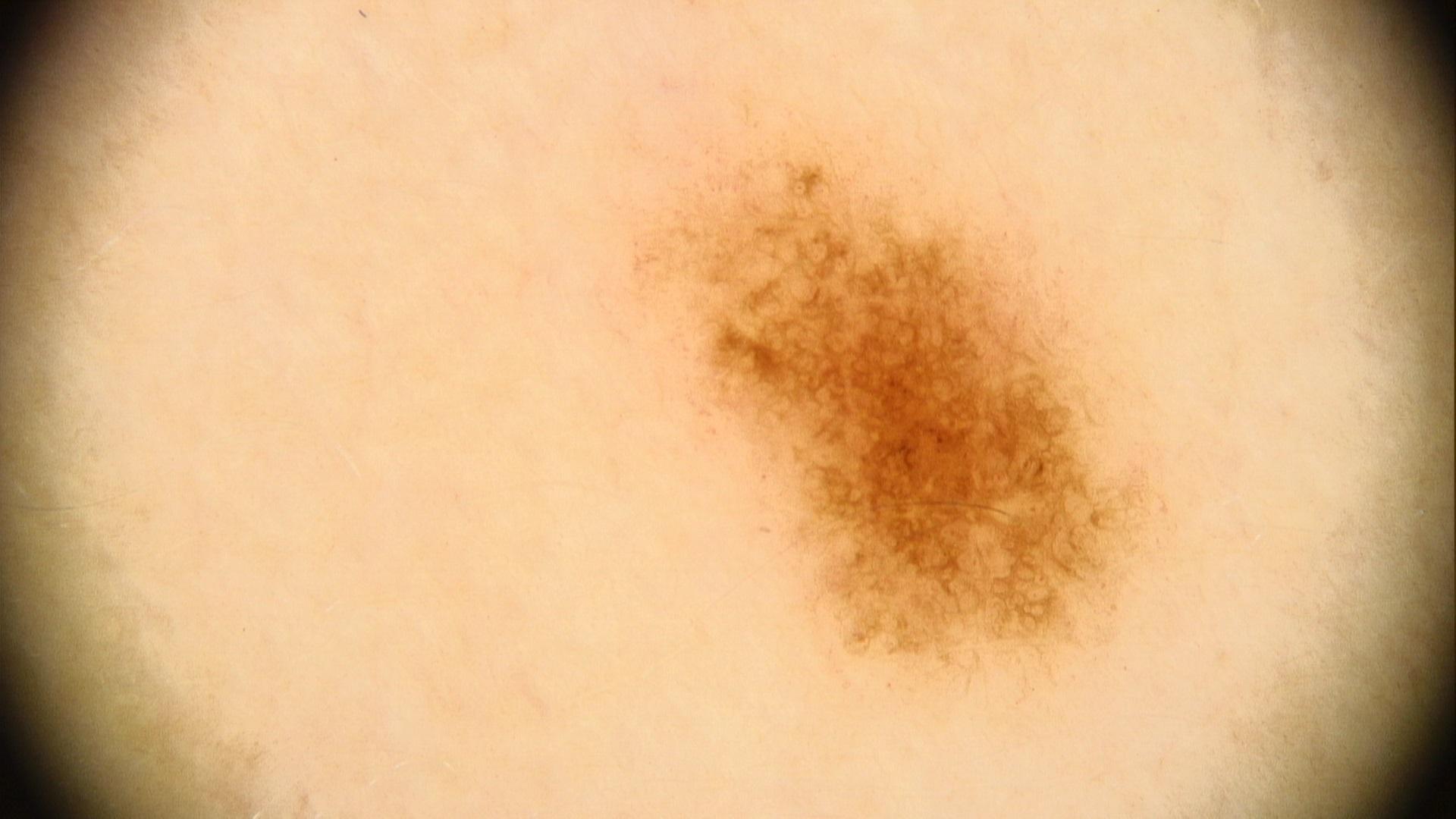subject = male, roughly 40 years of age | risk factors = a first-degree relative with melanoma | assessment = Nevus.